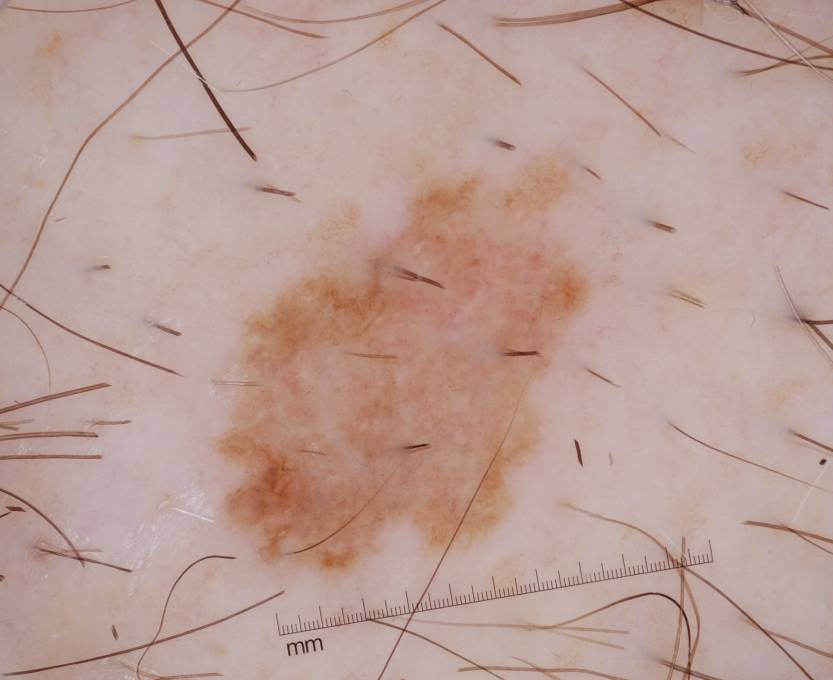Q: What kind of image is this?
A: dermoscopy of a skin lesion
Q: Lesion extent?
A: moderate
Q: Which dermoscopic features are absent?
A: pigment network, globules, negative network, milia-like cysts, and streaks
Q: What is the lesion's bounding box?
A: bbox=[213, 148, 597, 582]
Q: What is the diagnosis?
A: a melanoma